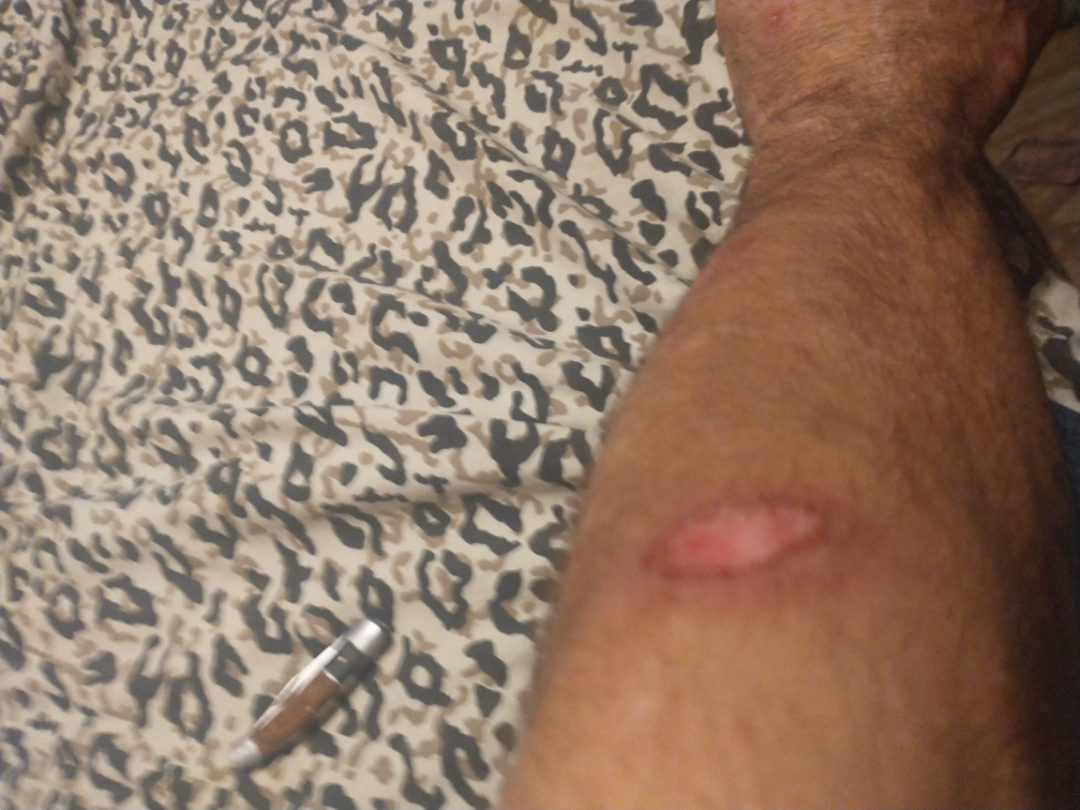Clinical context:
The photo was captured at an angle. The patient is 40–49, male. Located on the arm and leg.
Assessment:
On photographic review, consistent with Scar Condition.